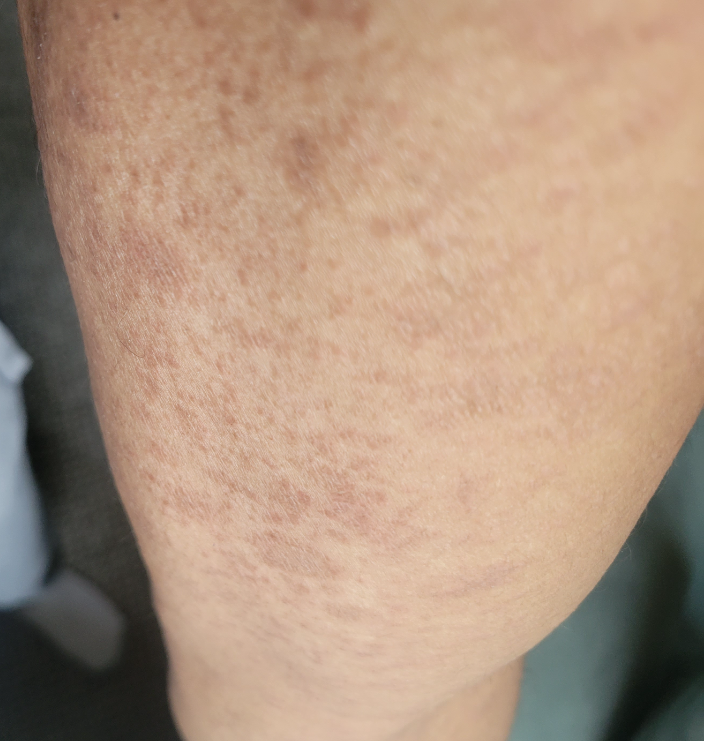Notes:
- history · one to four weeks
- affected area · front of the torso, back of the torso, head or neck and arm
- image framing · close-up
- patient's own categorization · a rash
- patient · male, age 30–39
- differential · single-reviewer assessment: Photodermatitis, Sunburn and Tinea Versicolor were each considered, in no particular order